A skin lesion imaged with a dermatoscope.
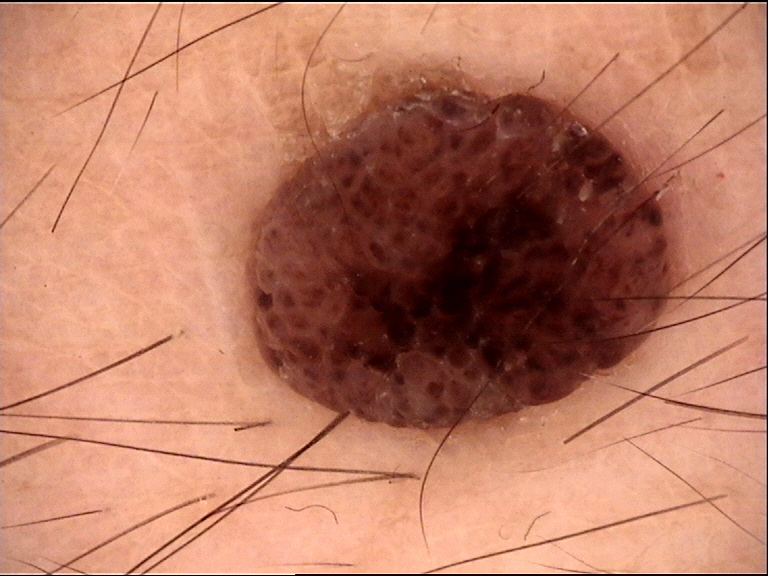Impression:
Consistent with a banal lesion — a dermal nevus.